A dermoscopy image of a single skin lesion; a male patient aged approximately 45.
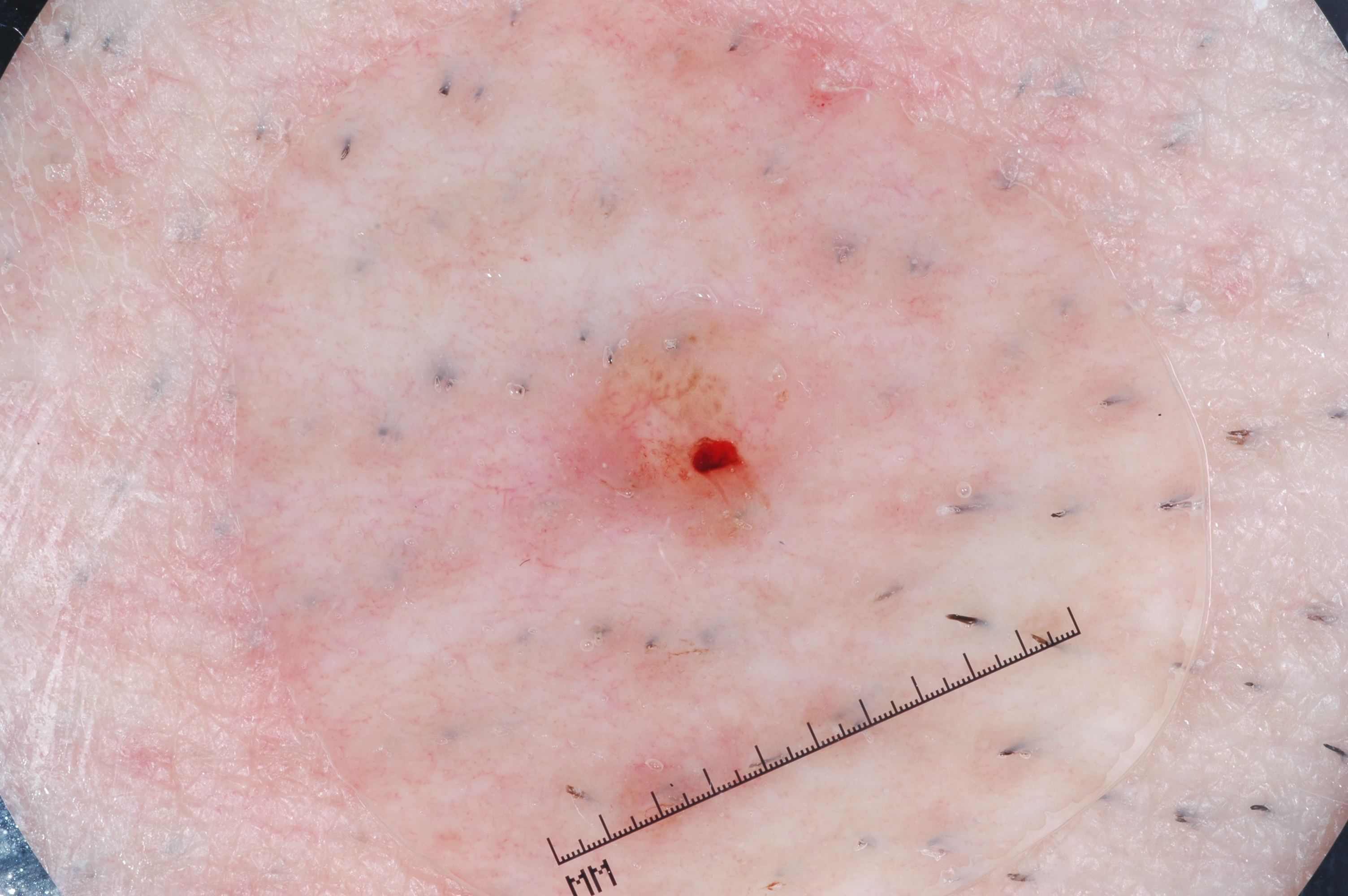dermoscopic findings = milia-like cysts, lesion extent = small, location = 472/297/841/577, impression = a melanocytic nevus.